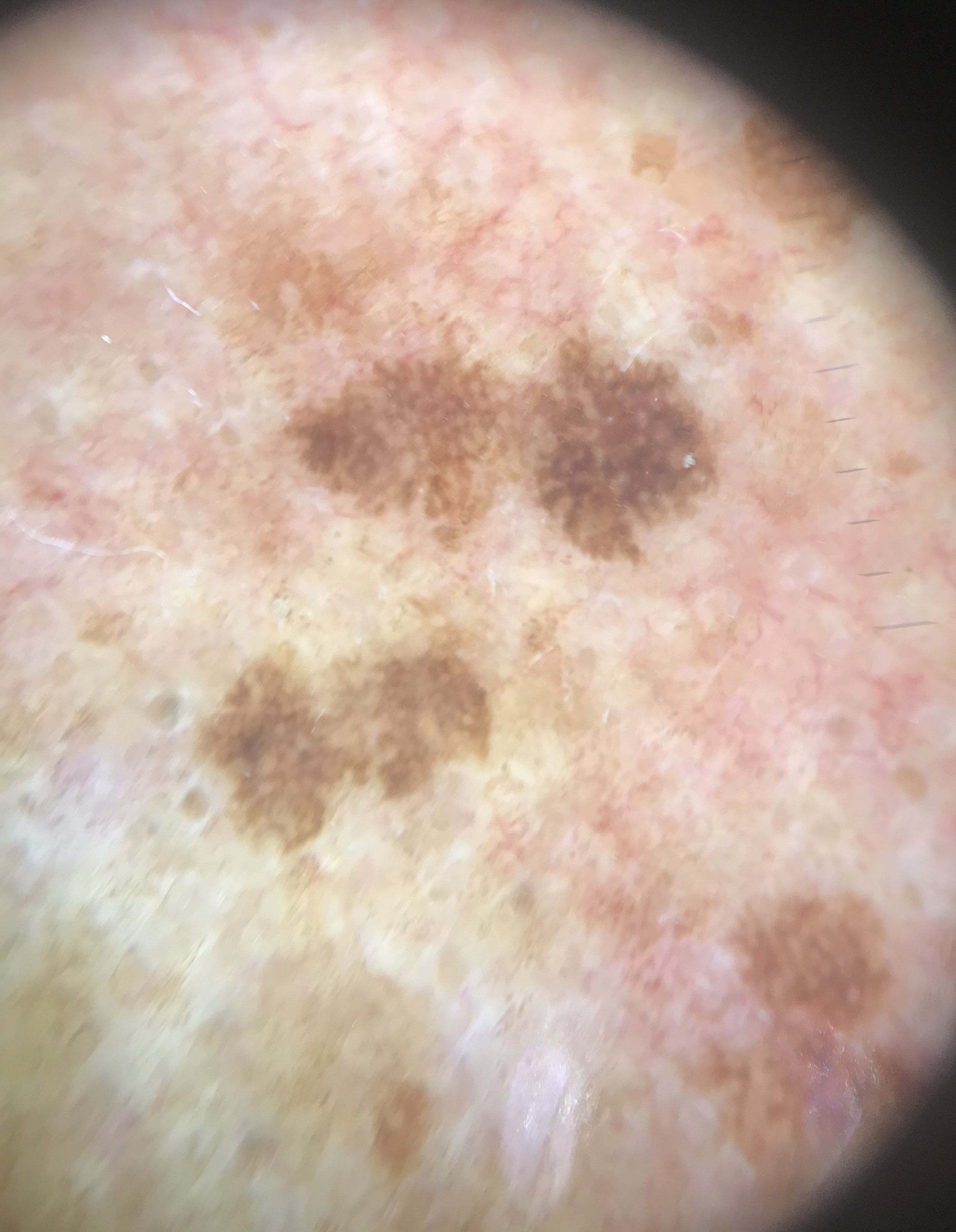This is a keratinocytic lesion. Diagnosed as a seborrheic keratosis.